A clinical photograph of a skin lesion.
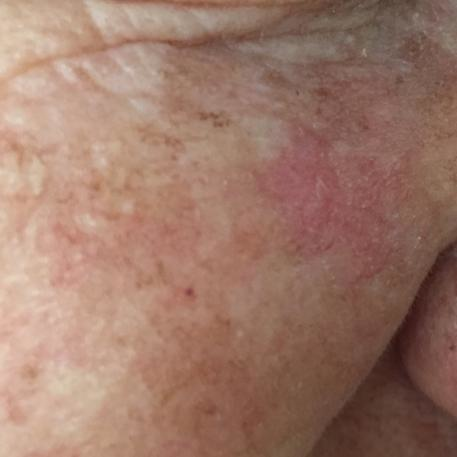{"lesion_location": "the face", "diagnosis": {"name": "actinic keratosis", "code": "ACK", "malignancy": "indeterminate", "confirmation": "clinical consensus"}}